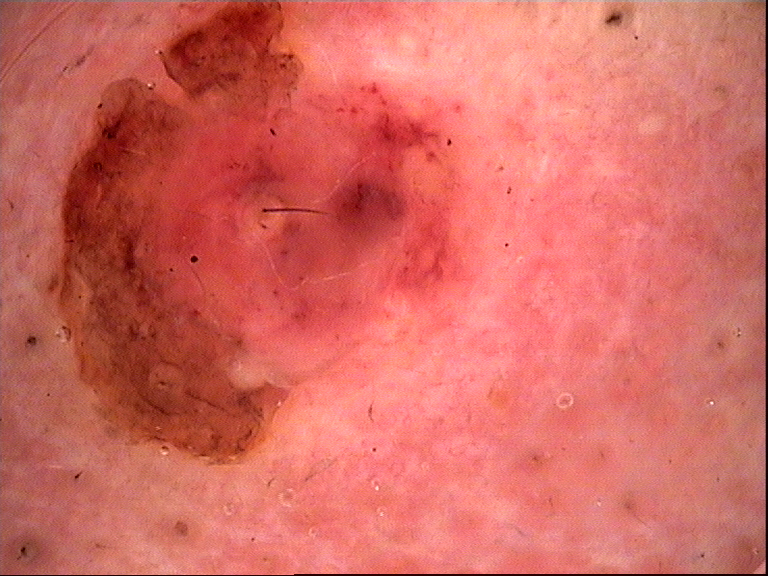<dermoscopy>
<image>dermatoscopy</image>
<diagnosis>
<name>squamous cell carcinoma</name>
<code>scc</code>
<malignancy>malignant</malignancy>
<super_class>non-melanocytic</super_class>
<confirmation>histopathology</confirmation>
</diagnosis>
</dermoscopy>